A close-up photograph. Female contributor, age 30–39. No constitutional symptoms were reported. The patient described the issue as a rash. The lesion is described as rough or flaky. Located on the back of the hand. Skin tone: Fitzpatrick skin type II.
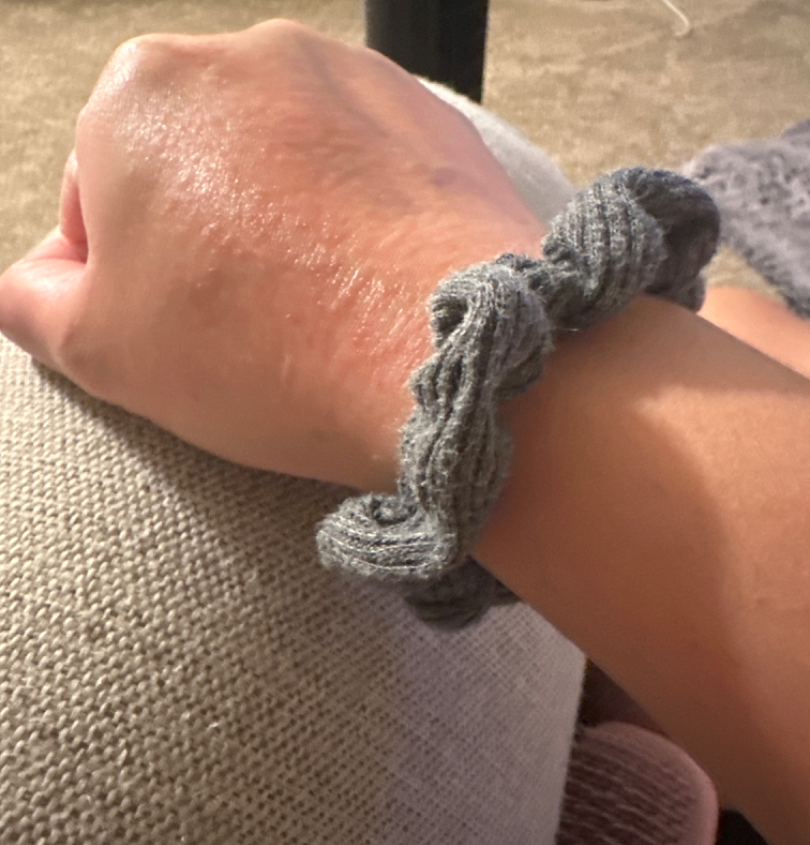| field | value |
|---|---|
| assessment | the favored diagnosis is Lichen nitidus; possibly Eczema |